The back of the torso is involved, reported duration is one to three months, the patient described the issue as skin that appeared healthy to them, the lesion is associated with itching, the photograph is a close-up of the affected area, skin tone: Fitzpatrick skin type IV; non-clinician graders estimated Monk skin tone scale 3 or 4, the contributor is male: 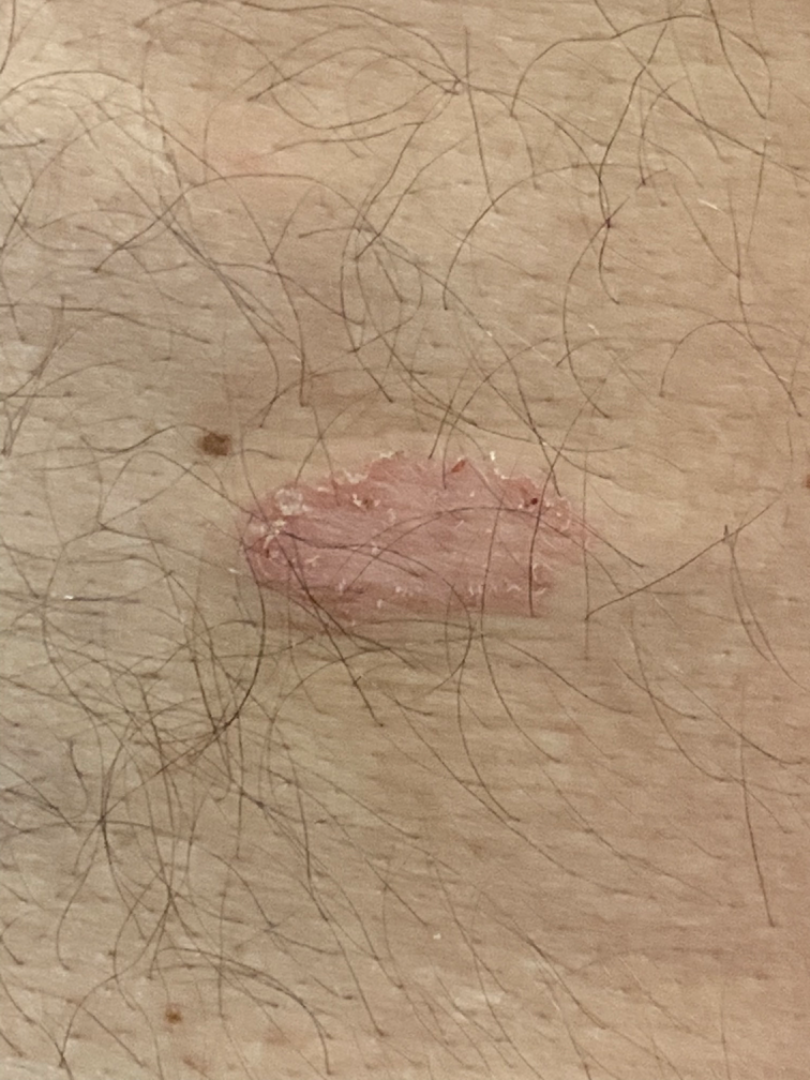impression = consistent with Pityriasis rosea.